The patient says their skin tans without first burning · dermoscopy of a skin lesion · the patient reports no personal history of cancer and no personal history of skin cancer · a male subject age 72 · collected as part of a research study, without a referral diagnosis · a moderate number of moles by the patient's own estimate — 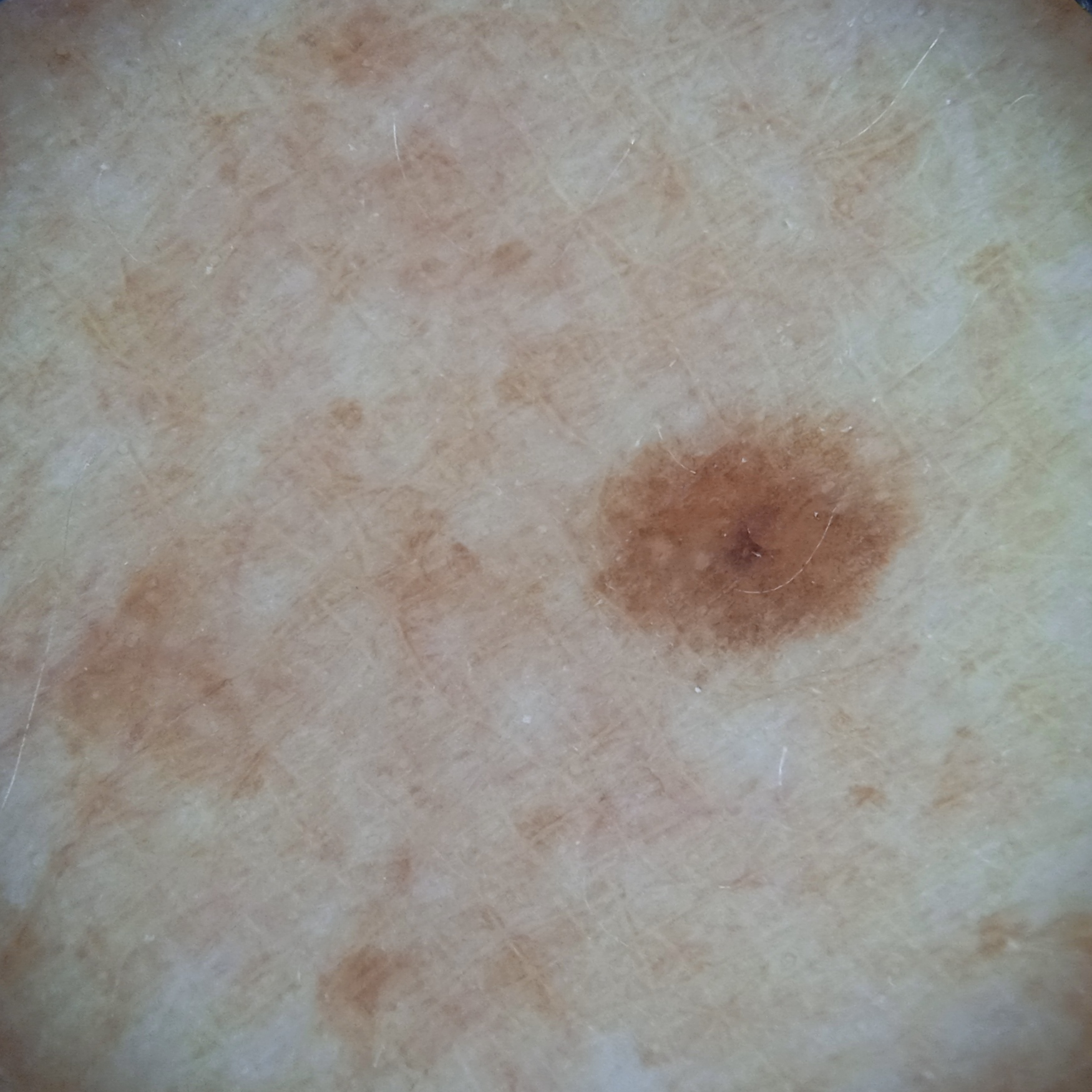The lesion is located on the back. The dermatologists' assessment was a melanocytic nevus.